The patient says their skin reddens painfully with sun exposure. Imaged for a research study, with no referral diagnosis recorded:
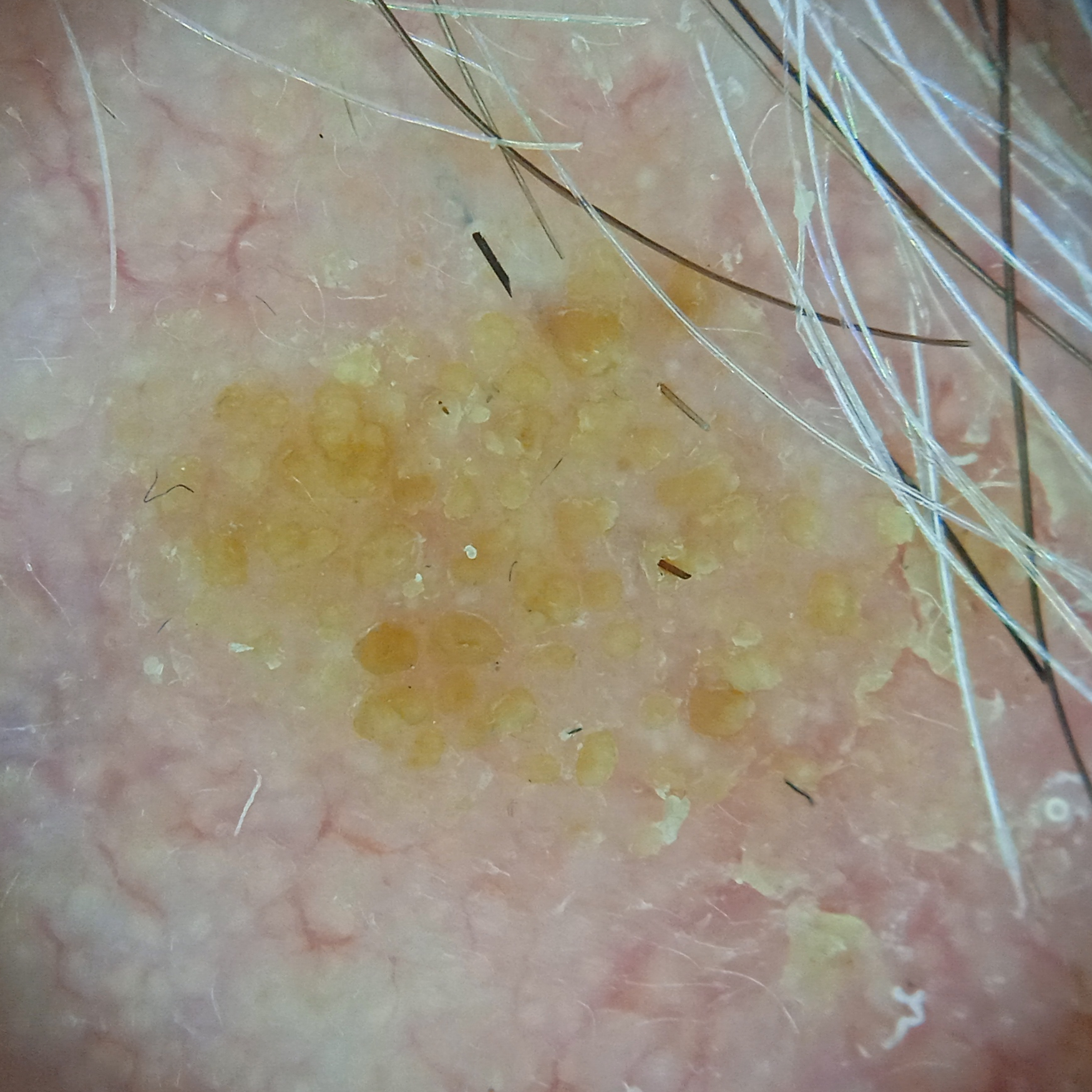body site: the face | diagnosis: seborrheic keratosis (dermatologist consensus).